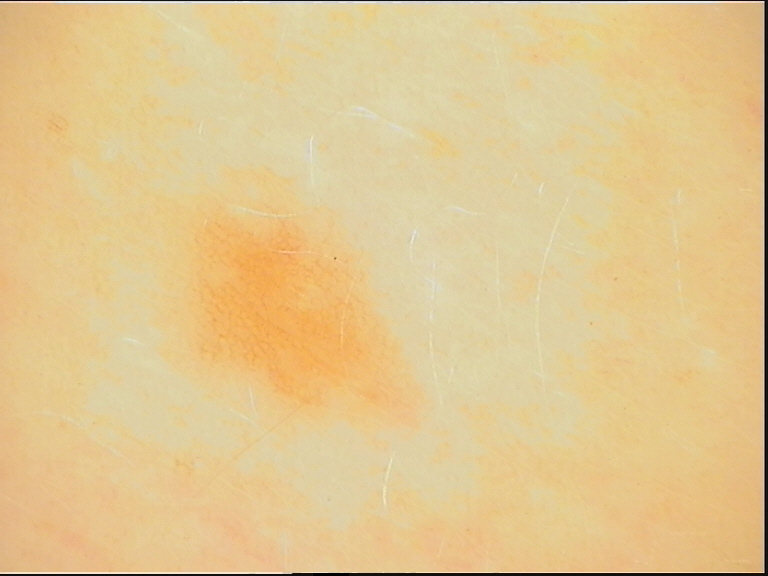Findings:
- image type: dermatoscopy
- diagnostic label: dysplastic junctional nevus (expert consensus)